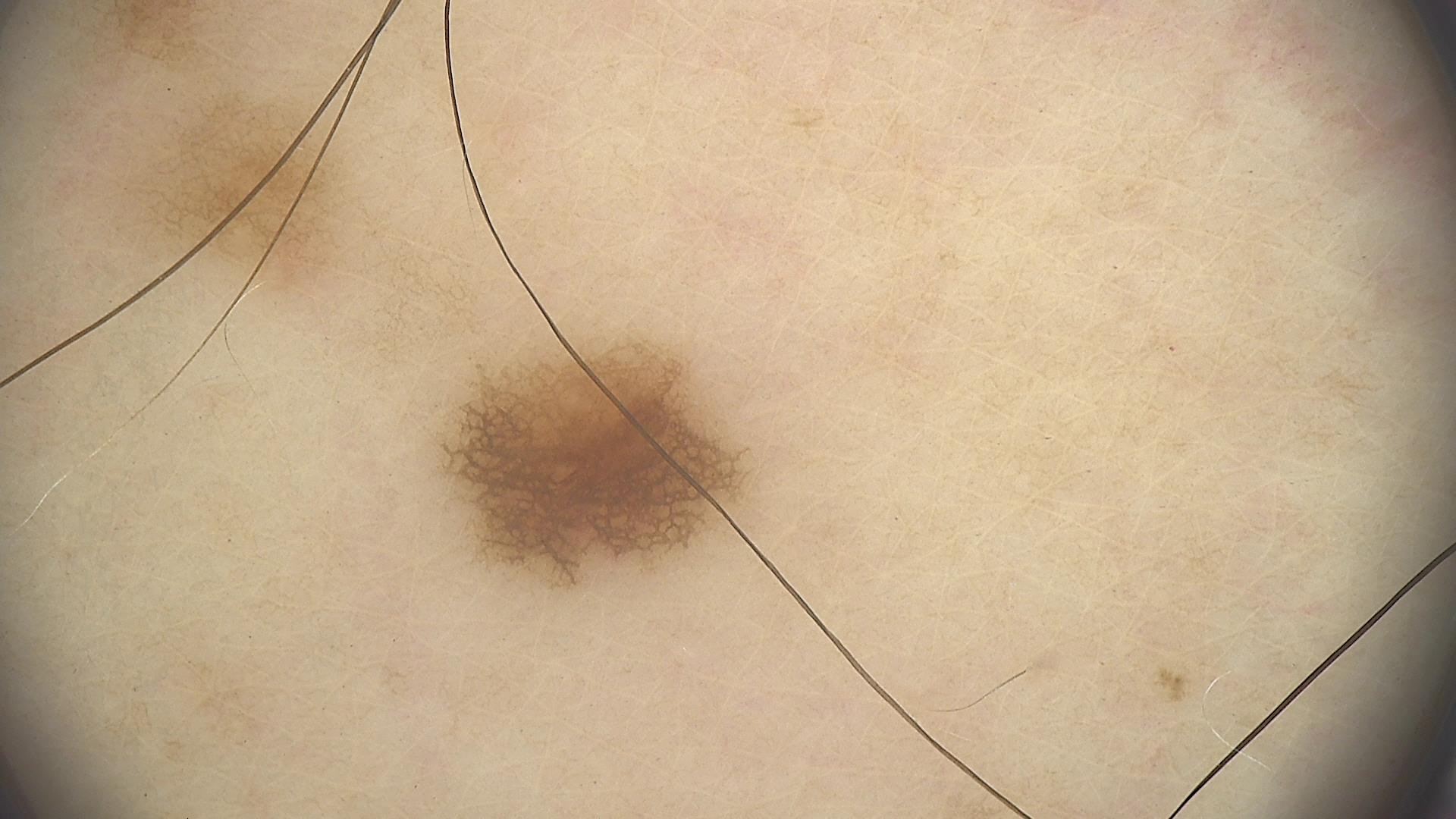Case:
– diagnosis · dysplastic junctional nevus (expert consensus)